The lesion involves the palm, the photograph is a close-up of the affected area: 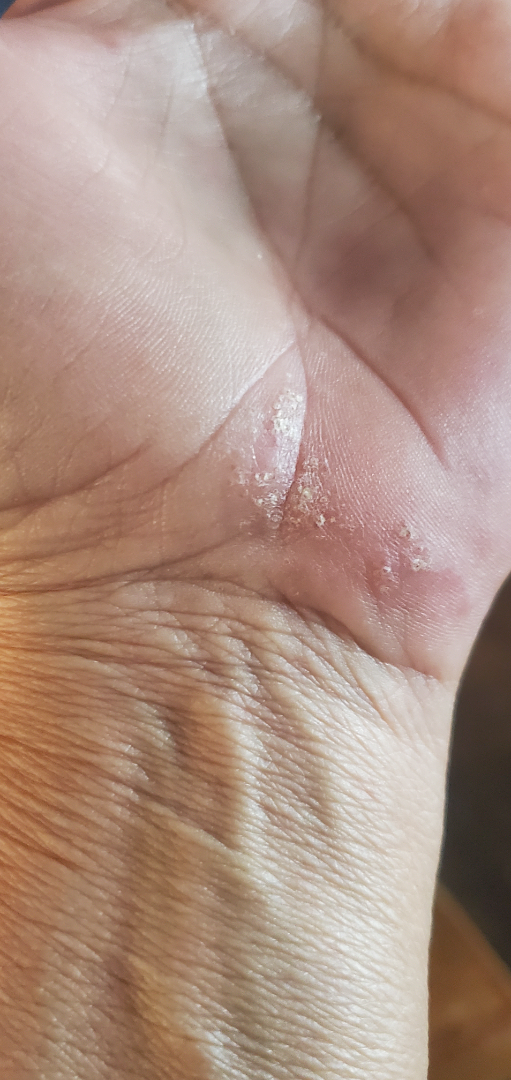The favored diagnosis is Eczema; with consideration of Allergic Contact Dermatitis; possibly Psoriasis.